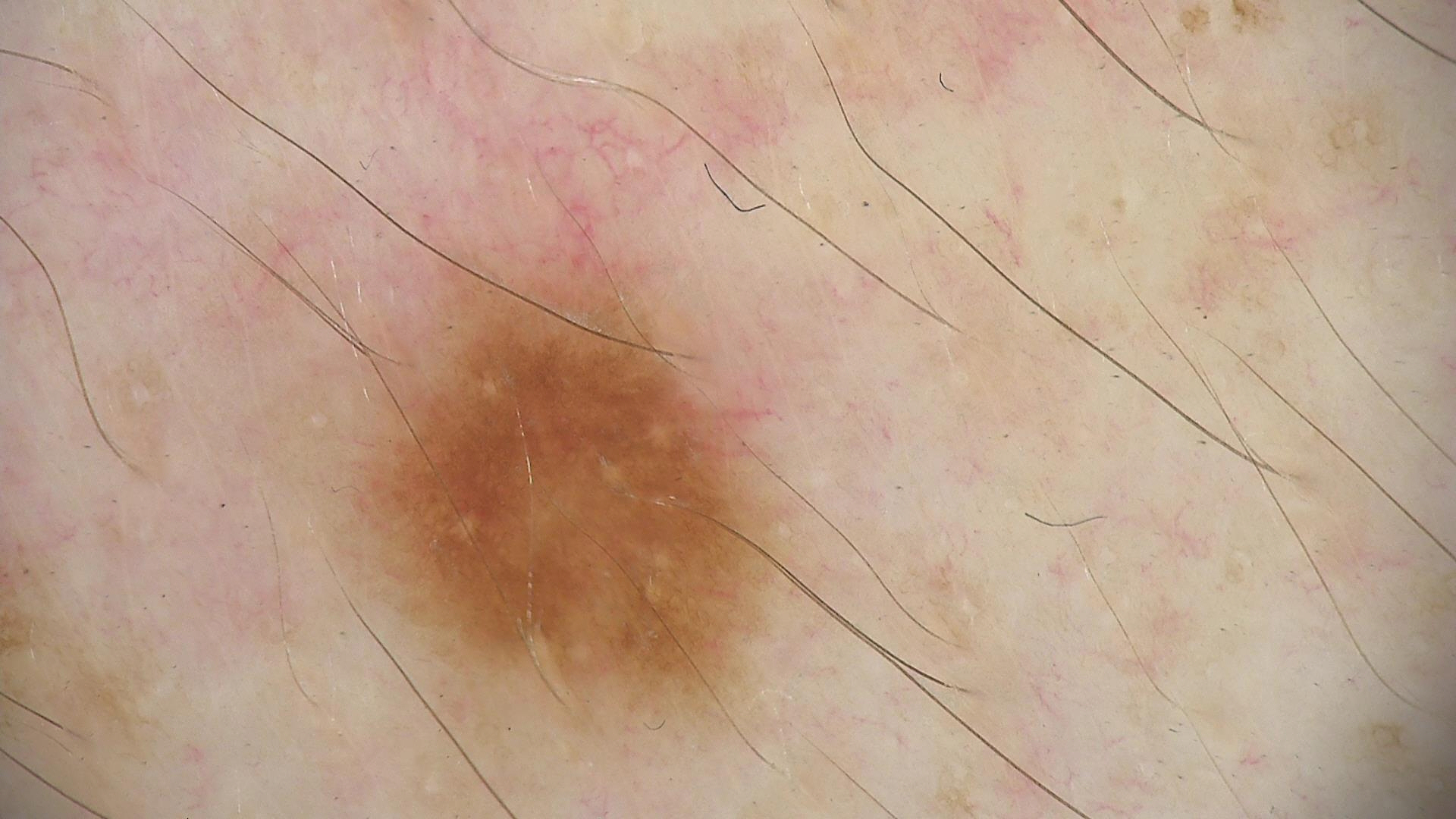{"diagnosis": {"name": "dysplastic junctional nevus", "code": "jd", "malignancy": "benign", "super_class": "melanocytic", "confirmation": "expert consensus"}}